A dermoscopic view of a skin lesion.
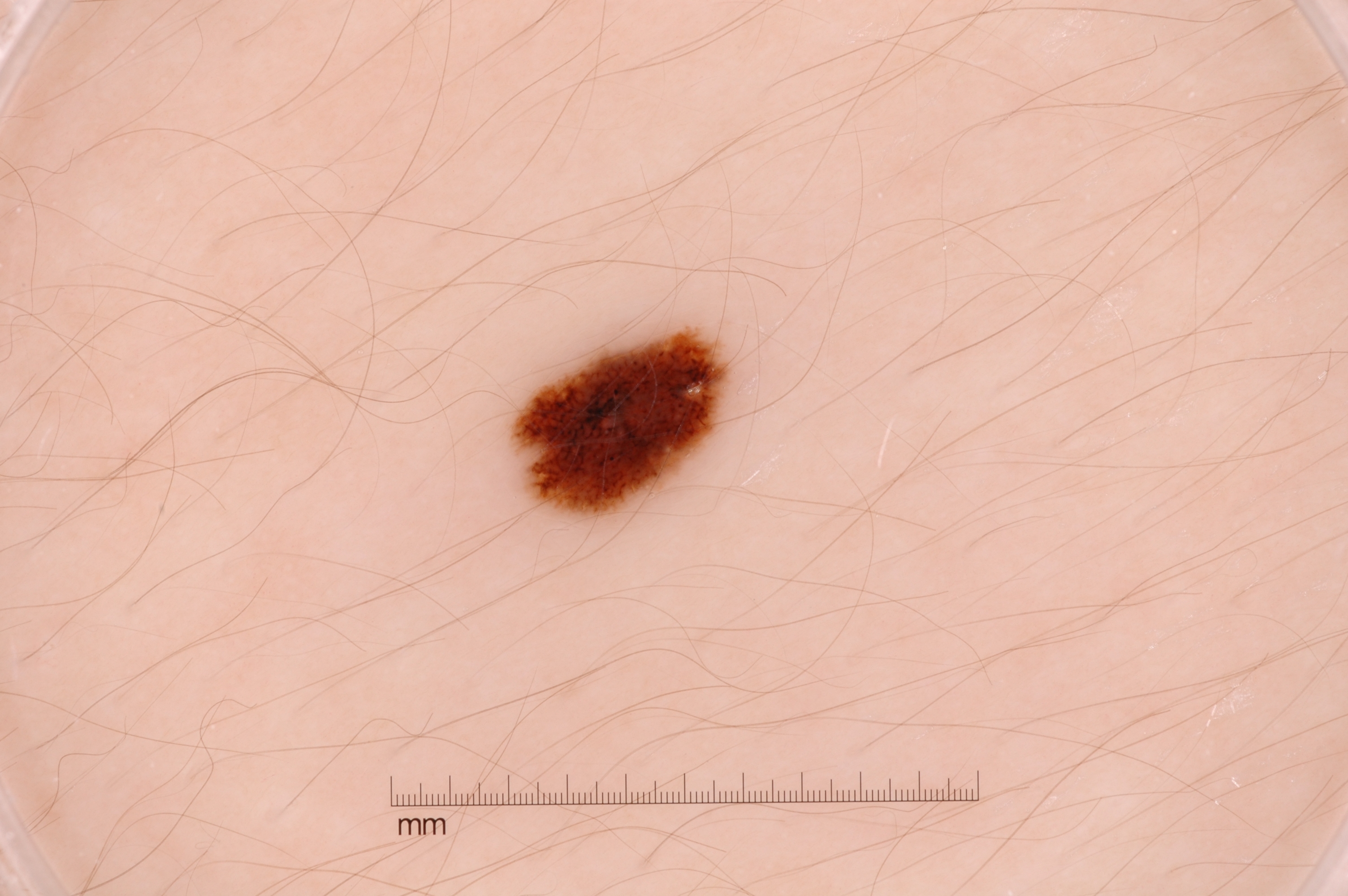Image and clinical context: The lesion occupies the region bbox(511, 331, 729, 522). The lesion takes up about 2% of the image. Dermoscopic review identifies pigment network; no milia-like cysts, streaks, or negative network. Impression: The lesion was assessed as a melanocytic nevus.